A skin lesion imaged with a dermatoscope.
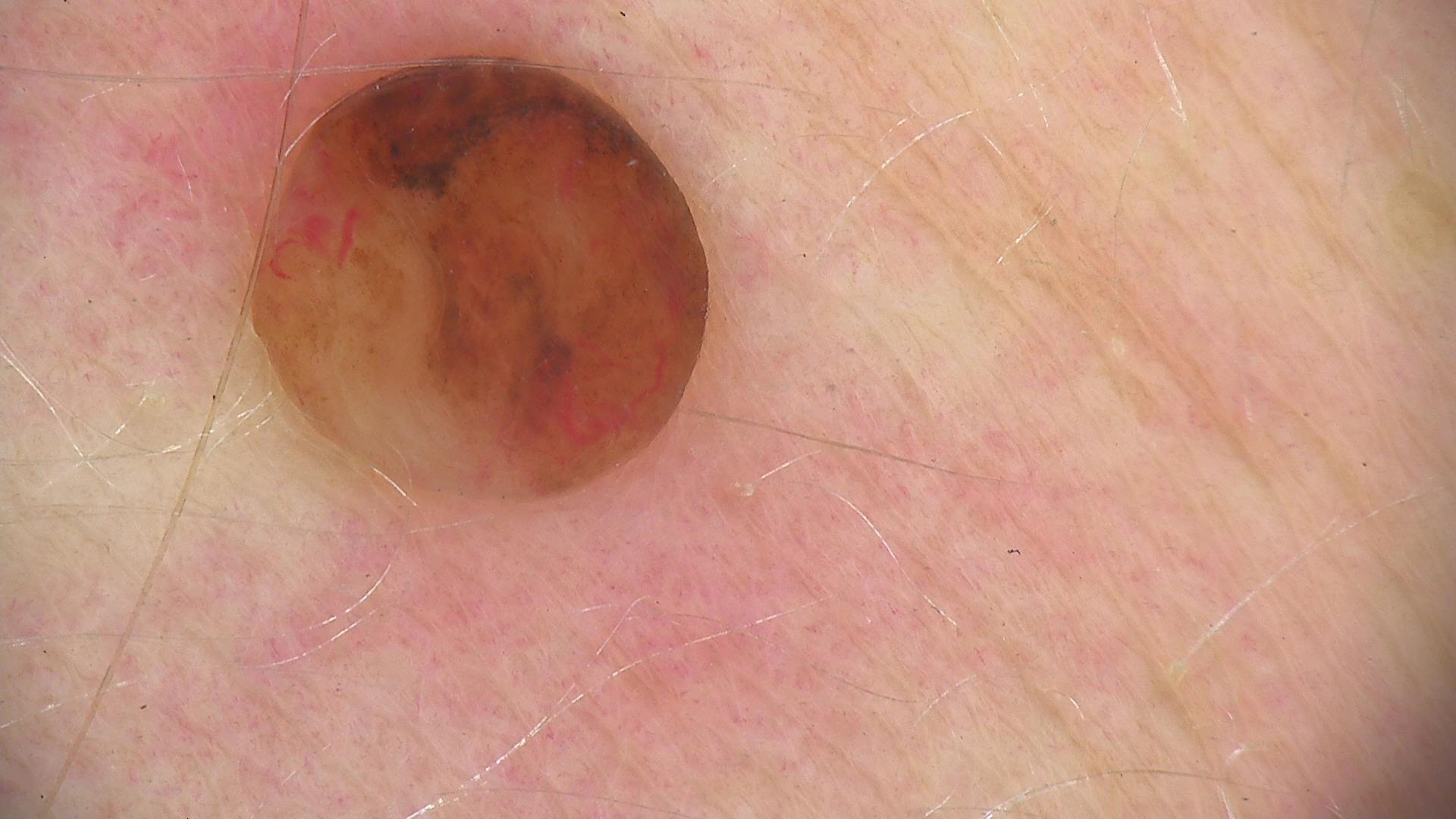Findings: This is a banal lesion. Impression: The diagnosis was a dermal nevus.